A female subject, approximately 60 years of age; a dermoscopic image of a skin lesion — 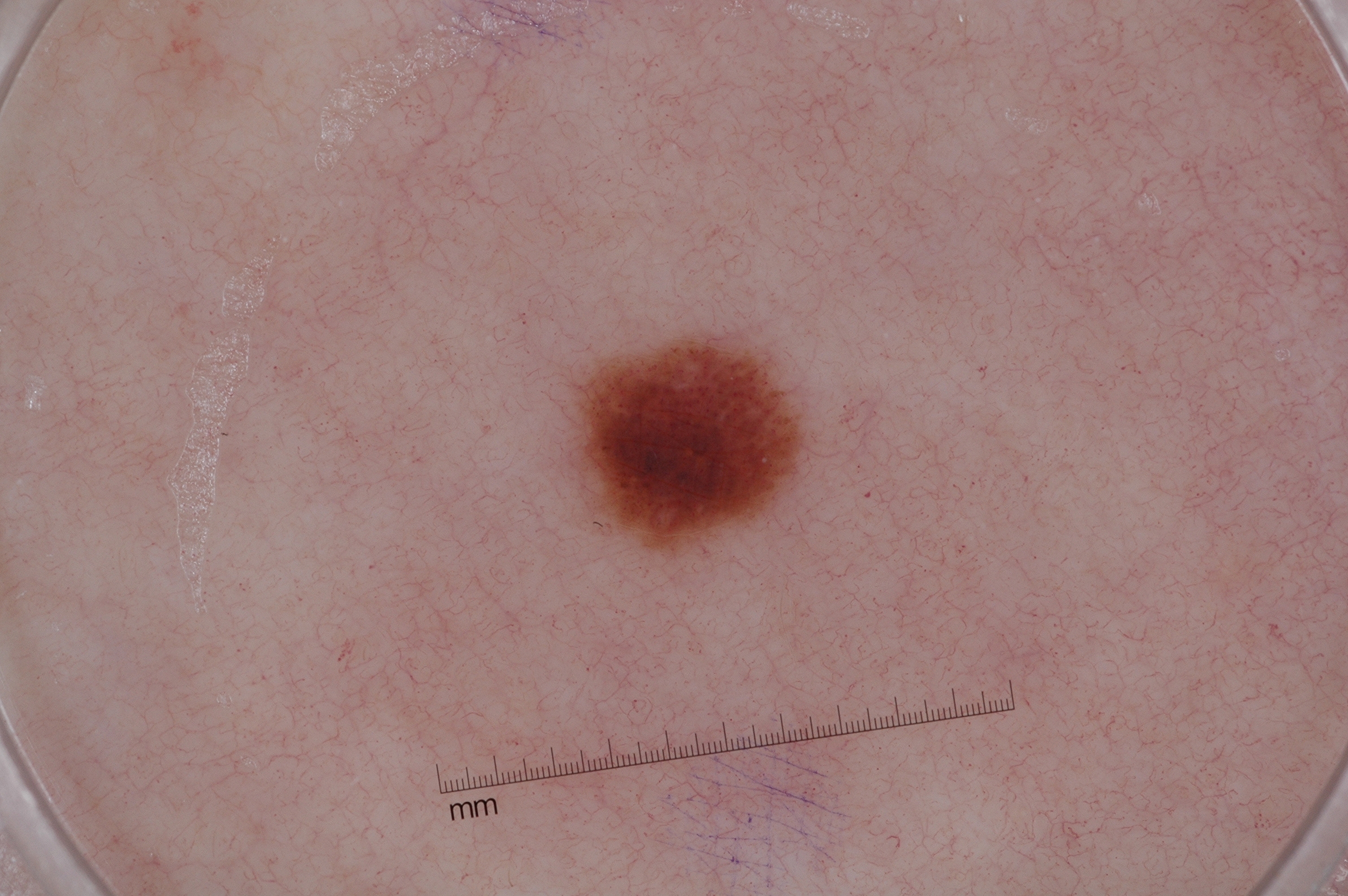absent dermoscopic features: milia-like cysts, streaks, pigment network, and negative network | lesion size: ~3% of the field | location: 572 335 809 559 | impression: a melanocytic nevus, a benign lesion.